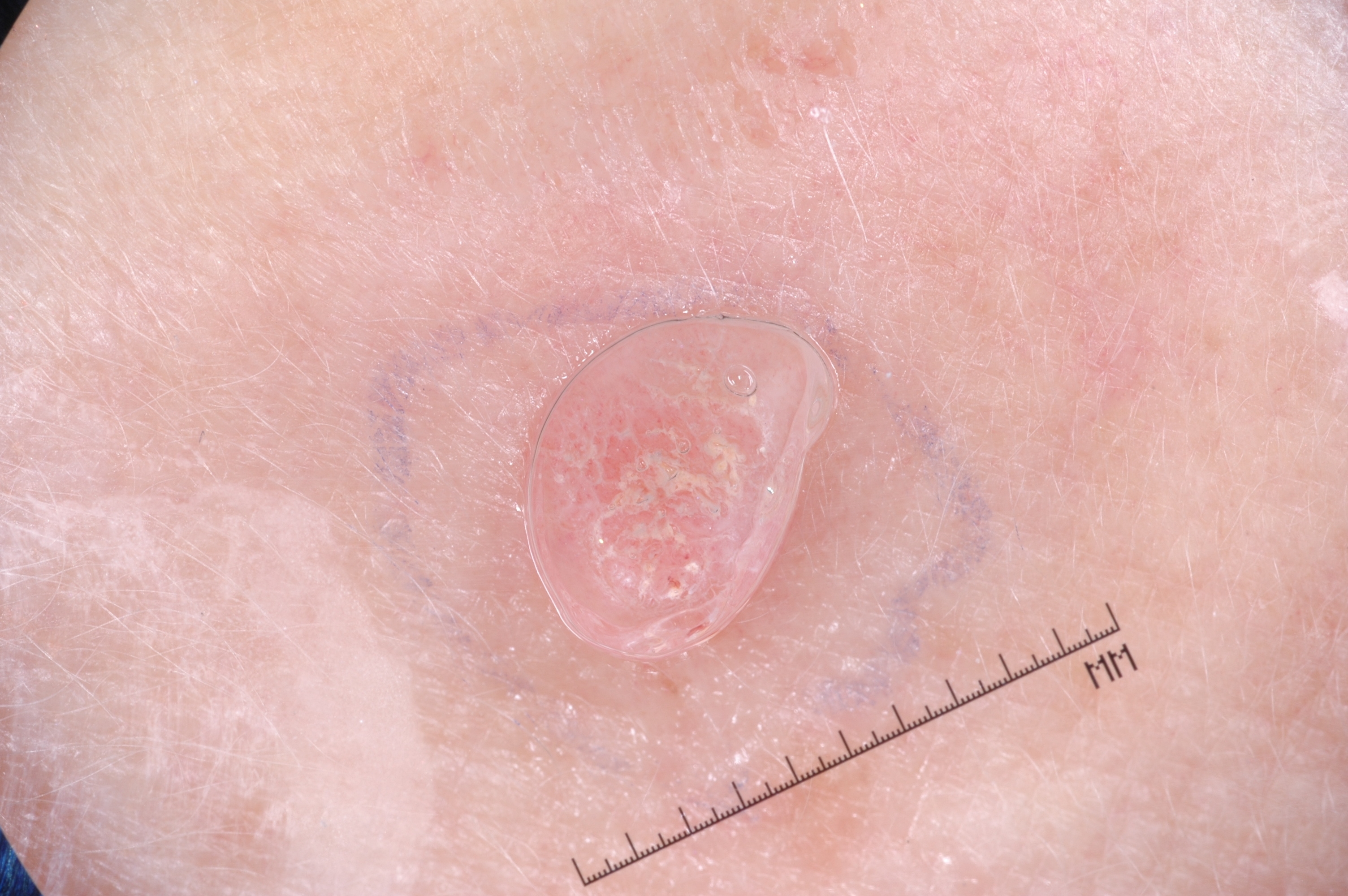modality — dermatoscopic image of a skin lesion
patient — female, in their 80s
lesion location — <box>539, 323, 805, 632</box>
dermoscopic pattern — milia-like cysts
diagnostic label — a seborrheic keratosis, a benign lesion